A dermoscopy image of a single skin lesion:
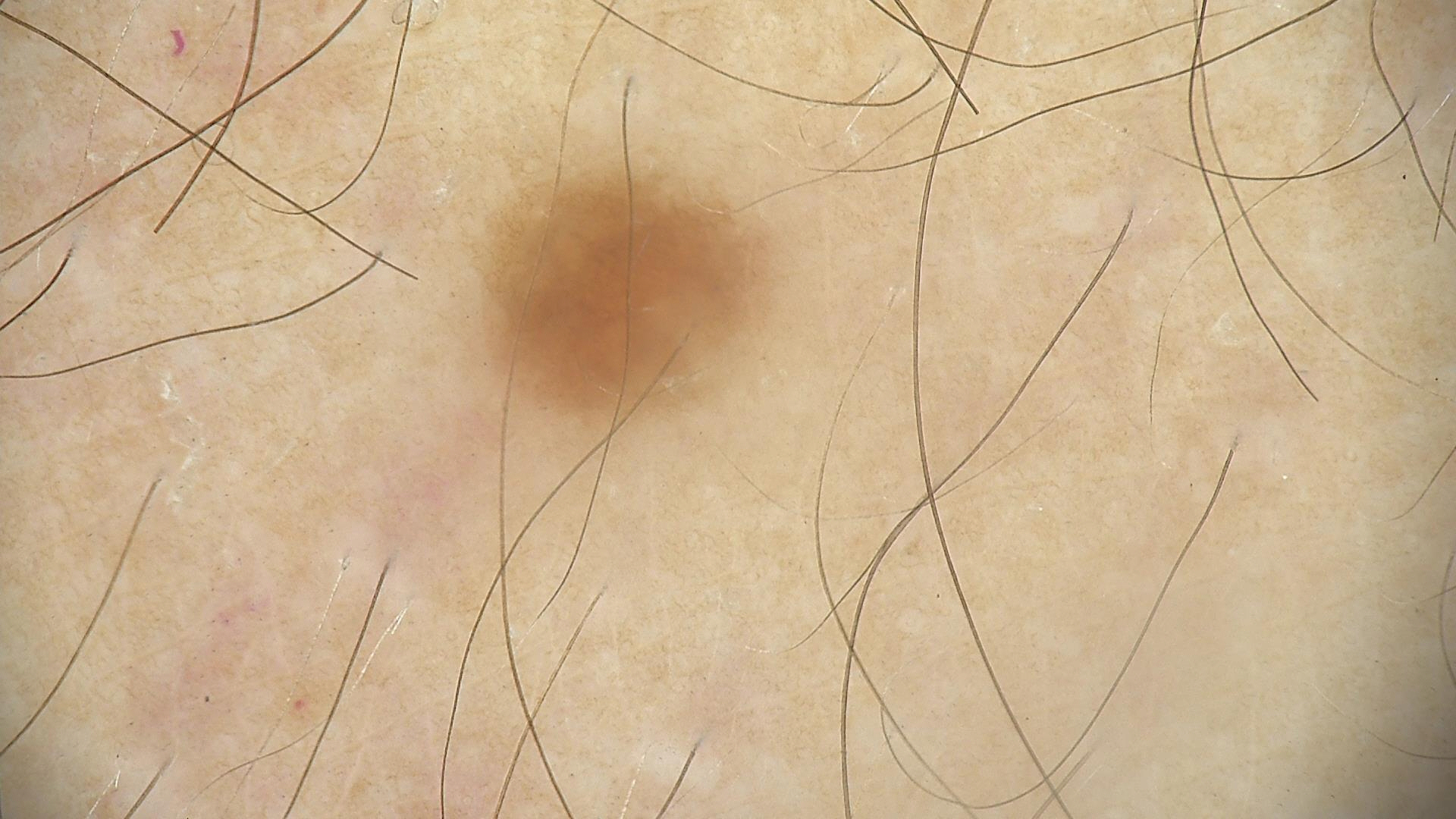| field | value |
|---|---|
| class | dysplastic junctional nevus (expert consensus) |